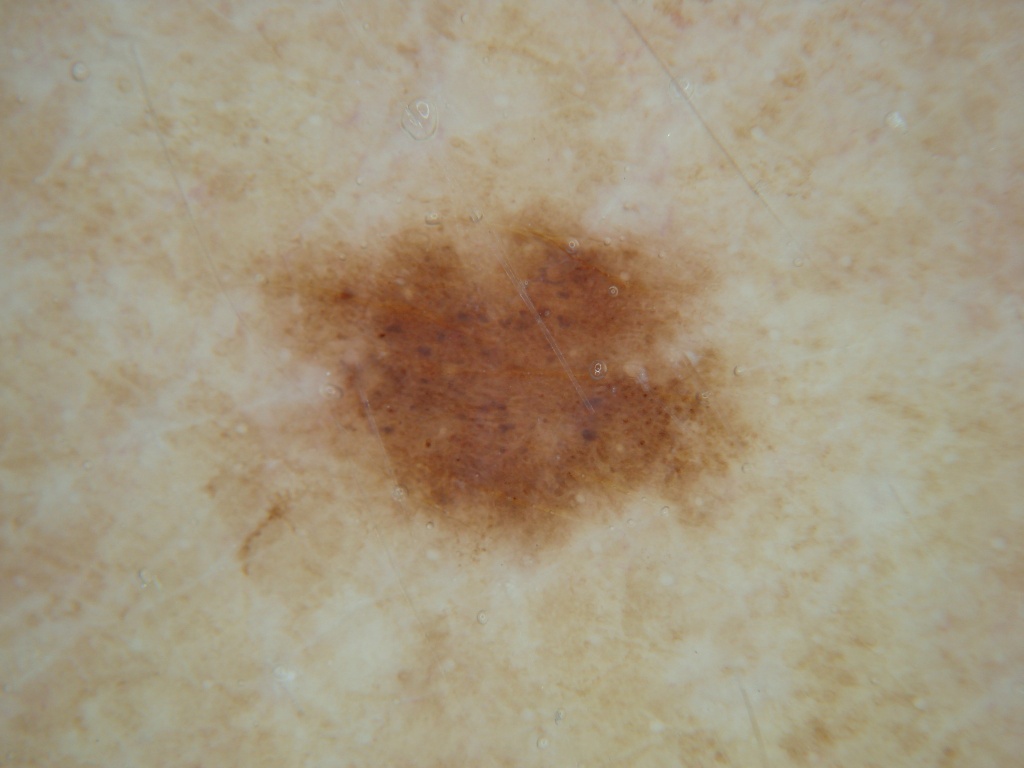image type: dermoscopy | lesion bbox: [250,200,744,552] | lesion size: moderate | features: globules | diagnosis: a benign lesion.